A skin lesion imaged with a dermatoscope: 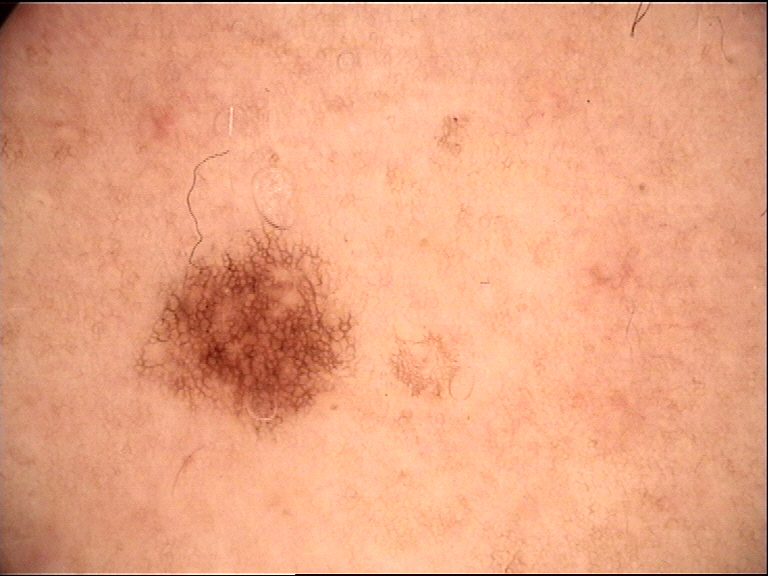Labeled as a dysplastic junctional nevus.